A dermoscopy image of a single skin lesion.
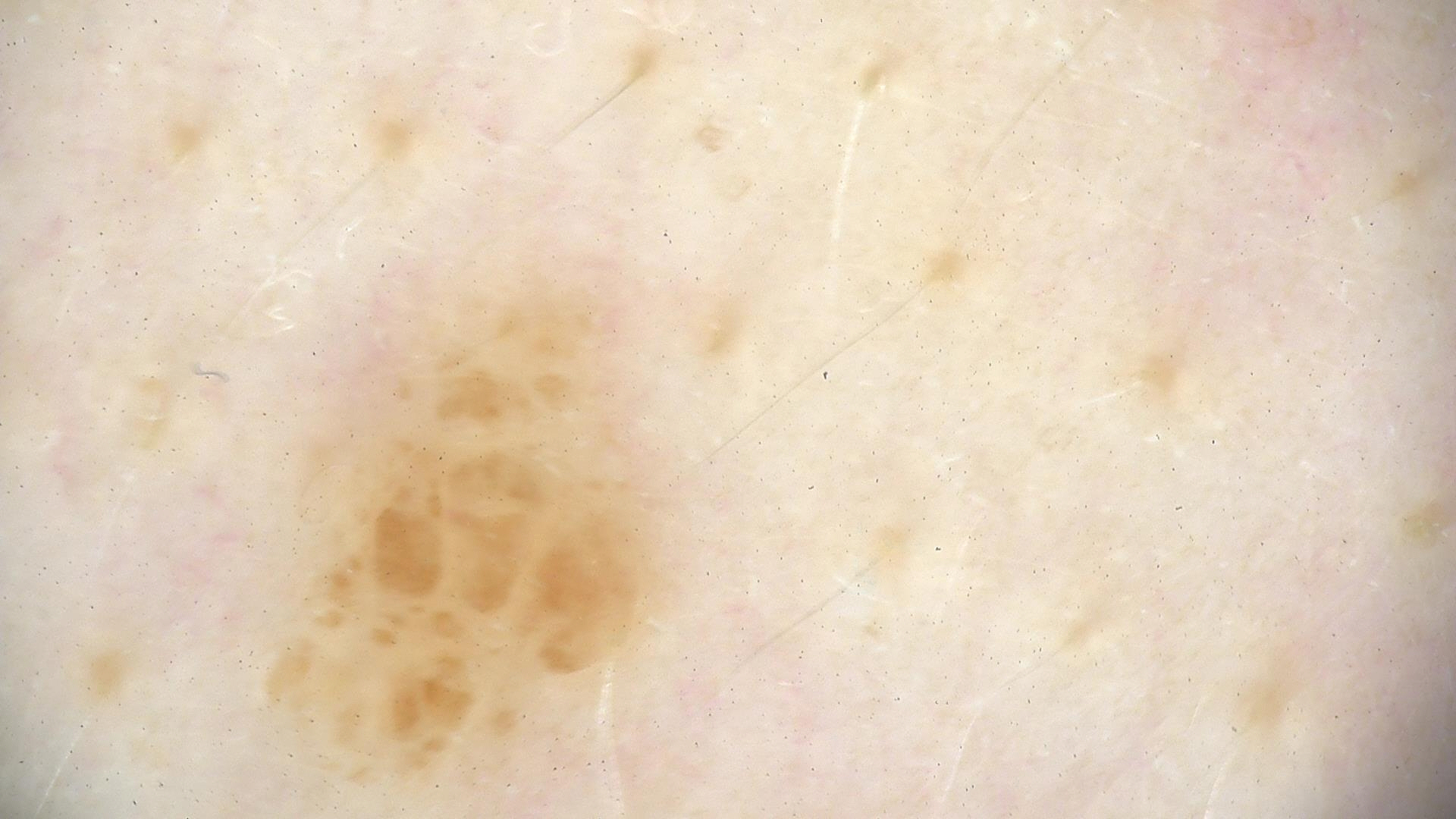diagnostic label = compound nevus (expert consensus).